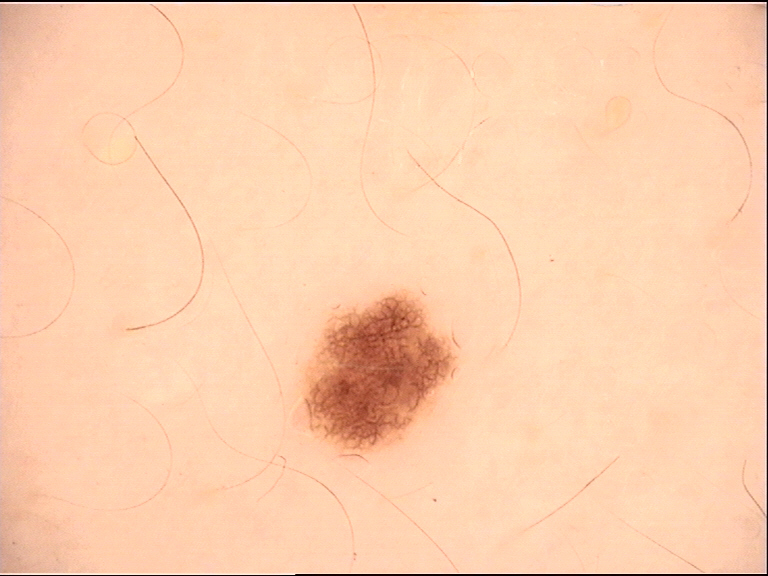Diagnosed as a dysplastic junctional nevus.